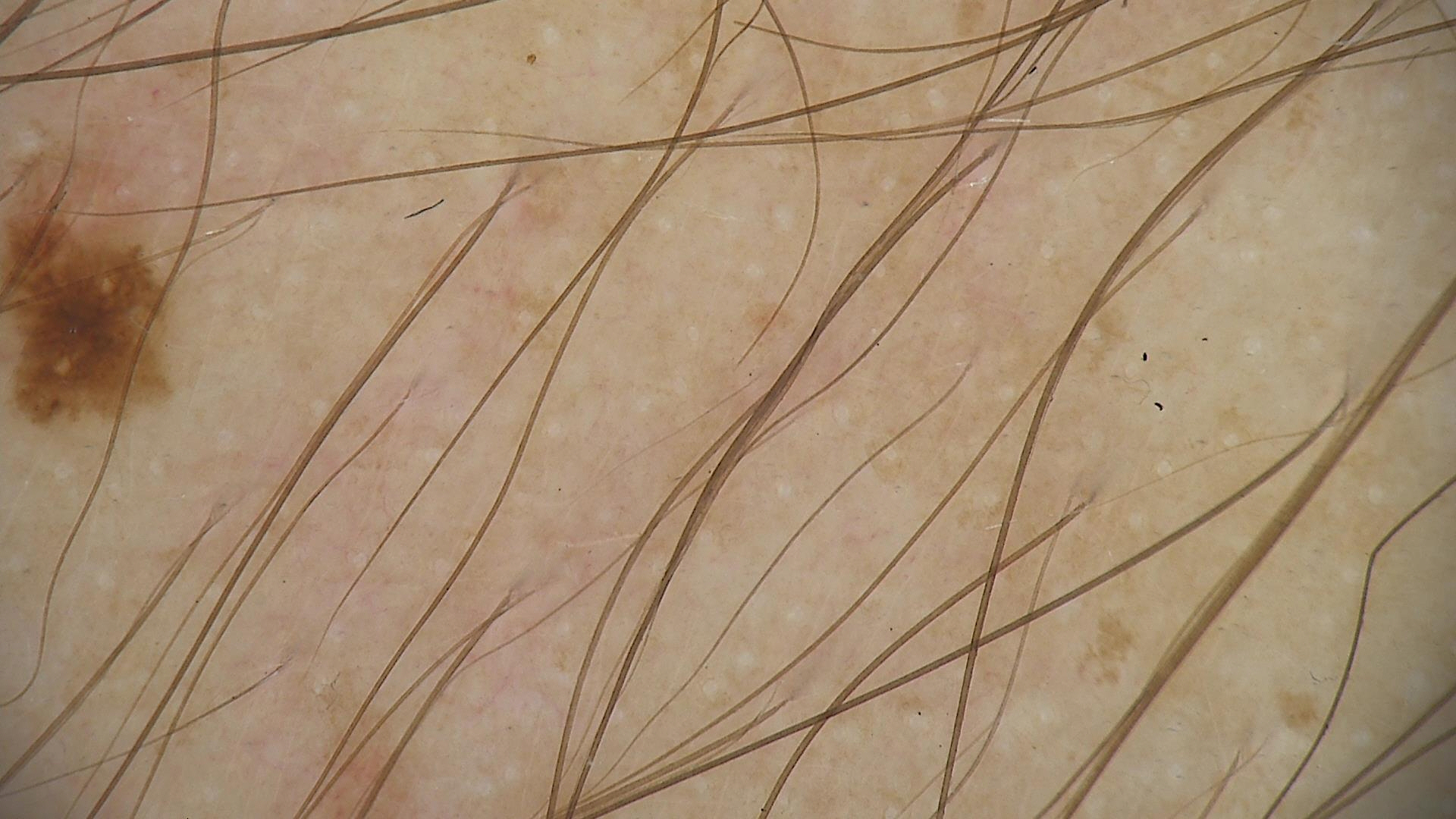Q: What is the diagnosis?
A: dysplastic junctional nevus (expert consensus)